A dermatoscopic image of a skin lesion.
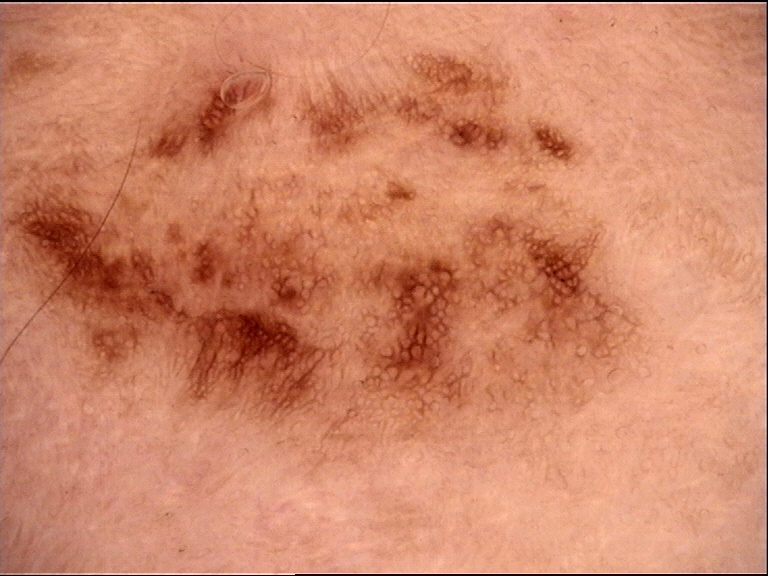lesion type: dysplastic, label: recurrent nevus (expert consensus).